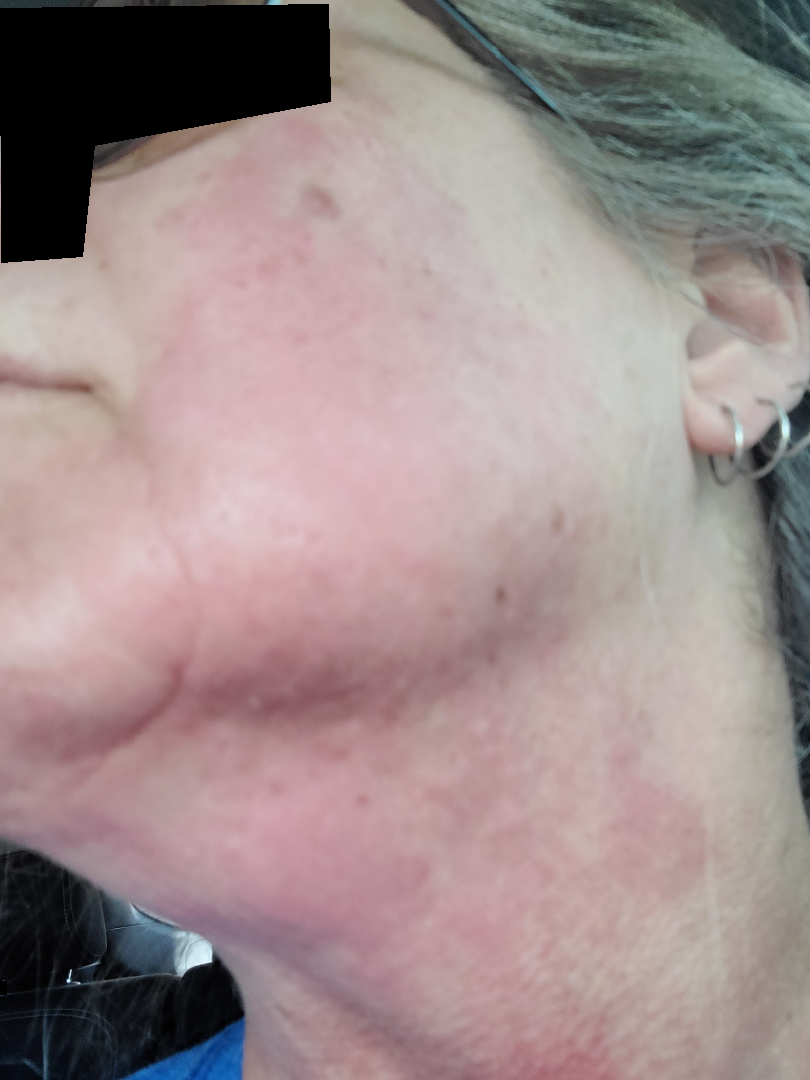The contributor is 60–69, female.
The photograph was taken at an angle.
Located on the head or neck.